The lesion is associated with bothersome appearance and itching · the lesion is described as raised or bumpy · the patient considered this a rash · skin tone: Fitzpatrick V; lay reviewers estimated Monk skin tone scale 3 or 5 (two reviewer pools disagreed) · this is a close-up image · the lesion involves the front of the torso, arm, back of the torso and leg: 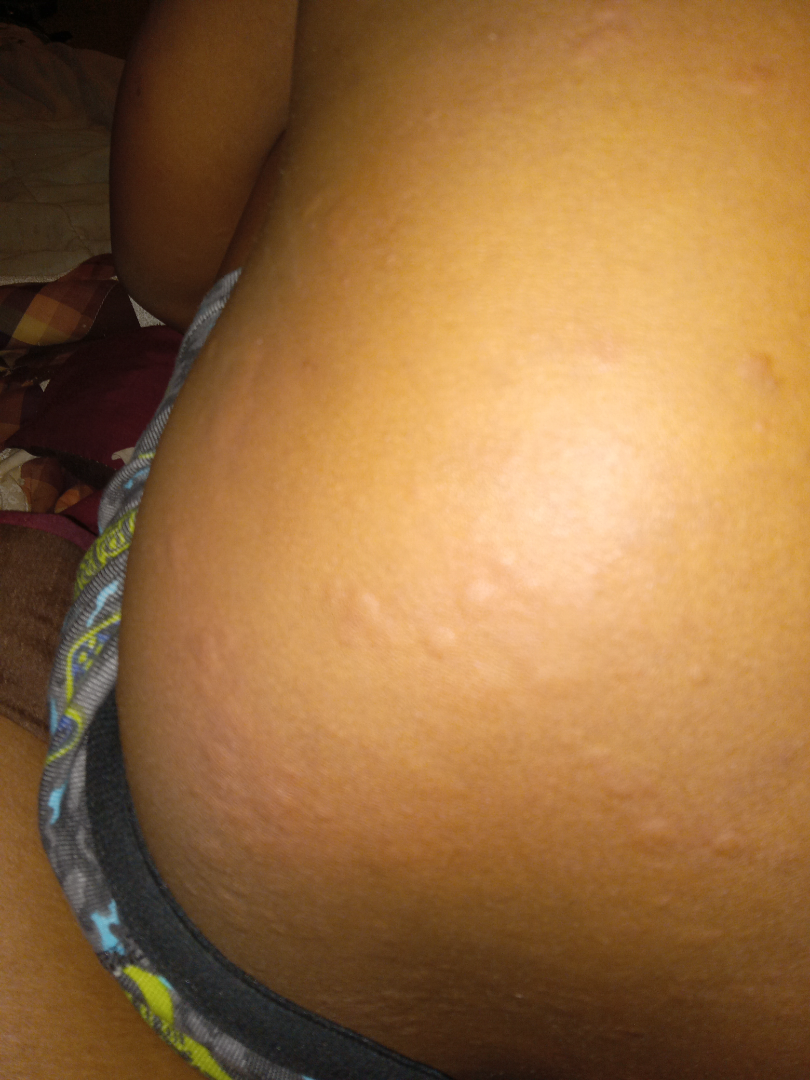dermatologist impression — Urticaria (most likely).